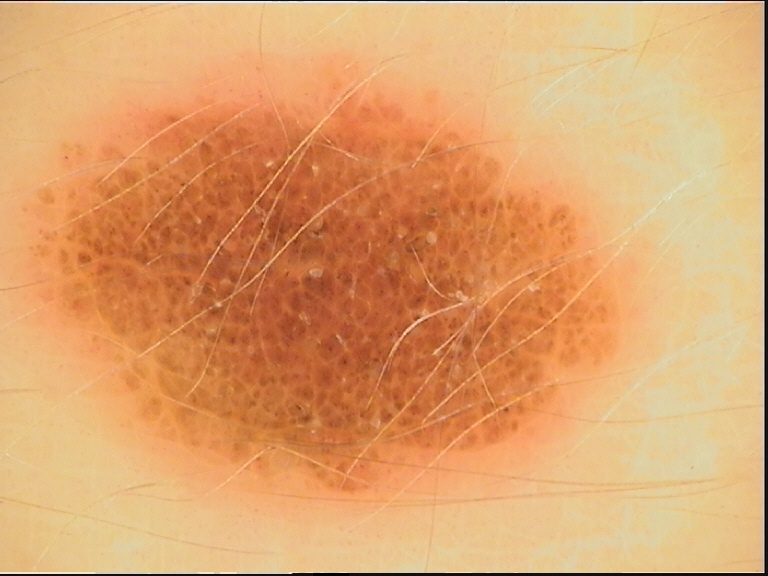Case: Dermoscopy of a skin lesion. Impression: Classified as a benign lesion — a dysplastic compound nevus.